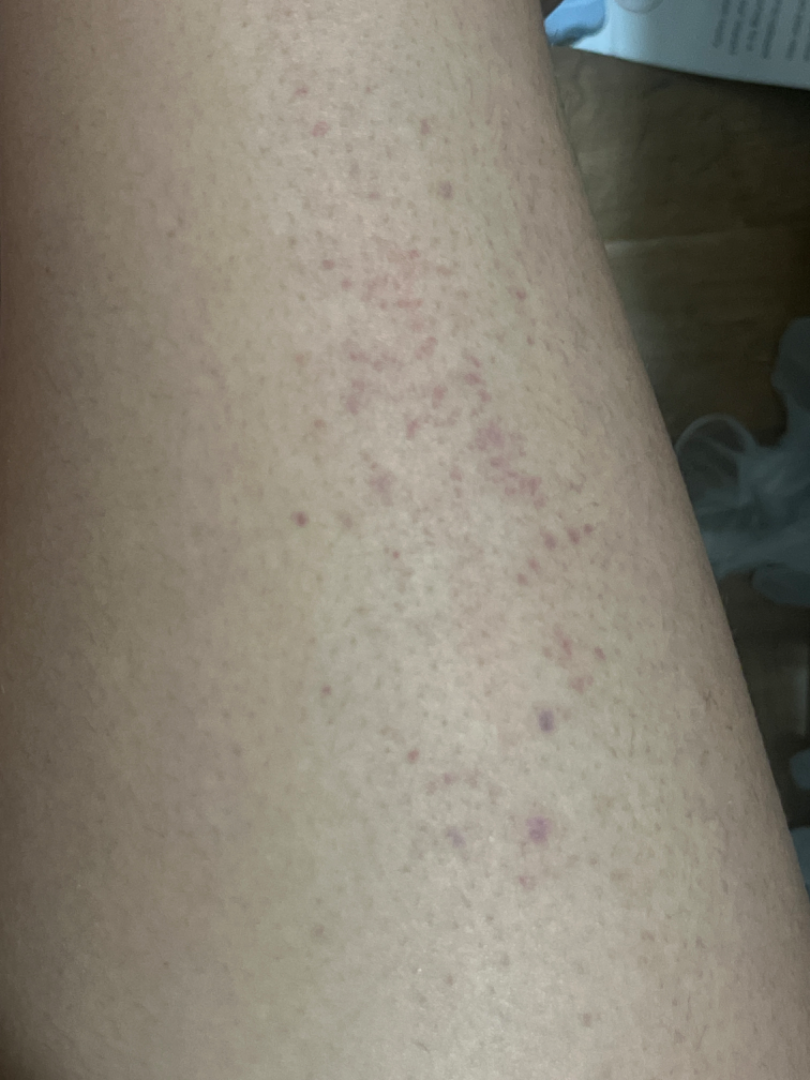{"assessment": "indeterminate from the photograph"}